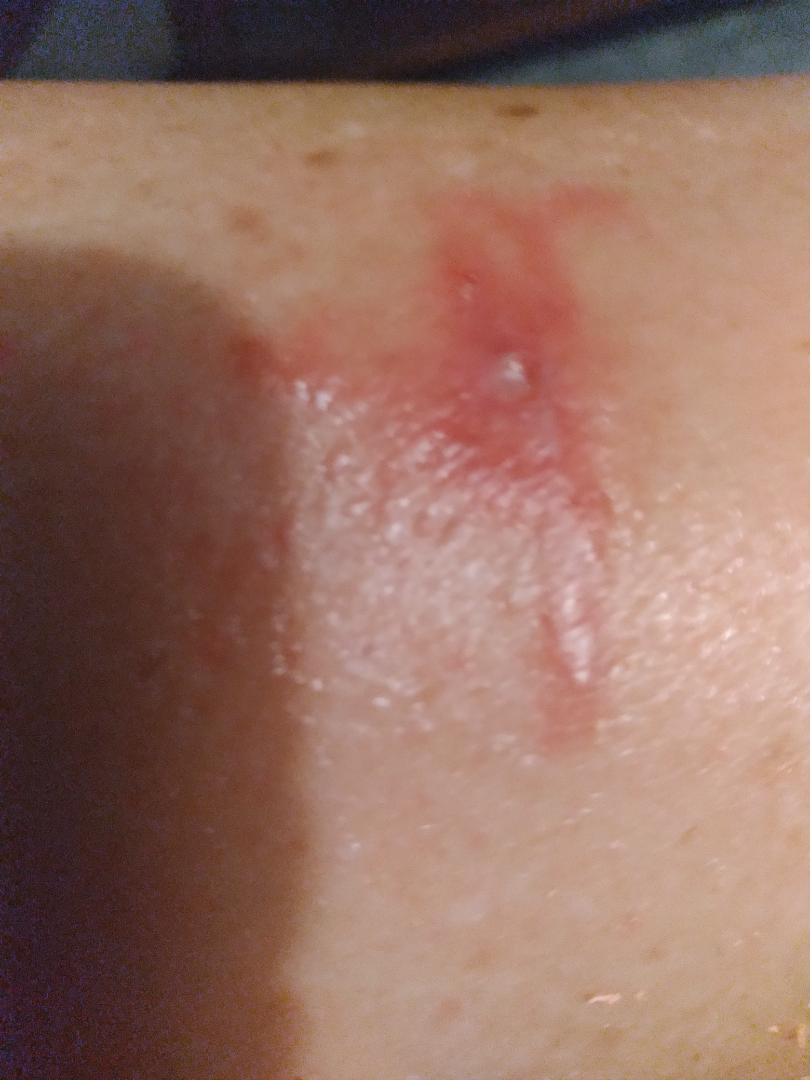Impression:
No differential diagnosis could be assigned on photographic review.